A contact-polarized dermoscopy image of a skin lesion. A female subject approximately 35 years of age. The chart records no melanoma in first-degree relatives and no prior melanoma — 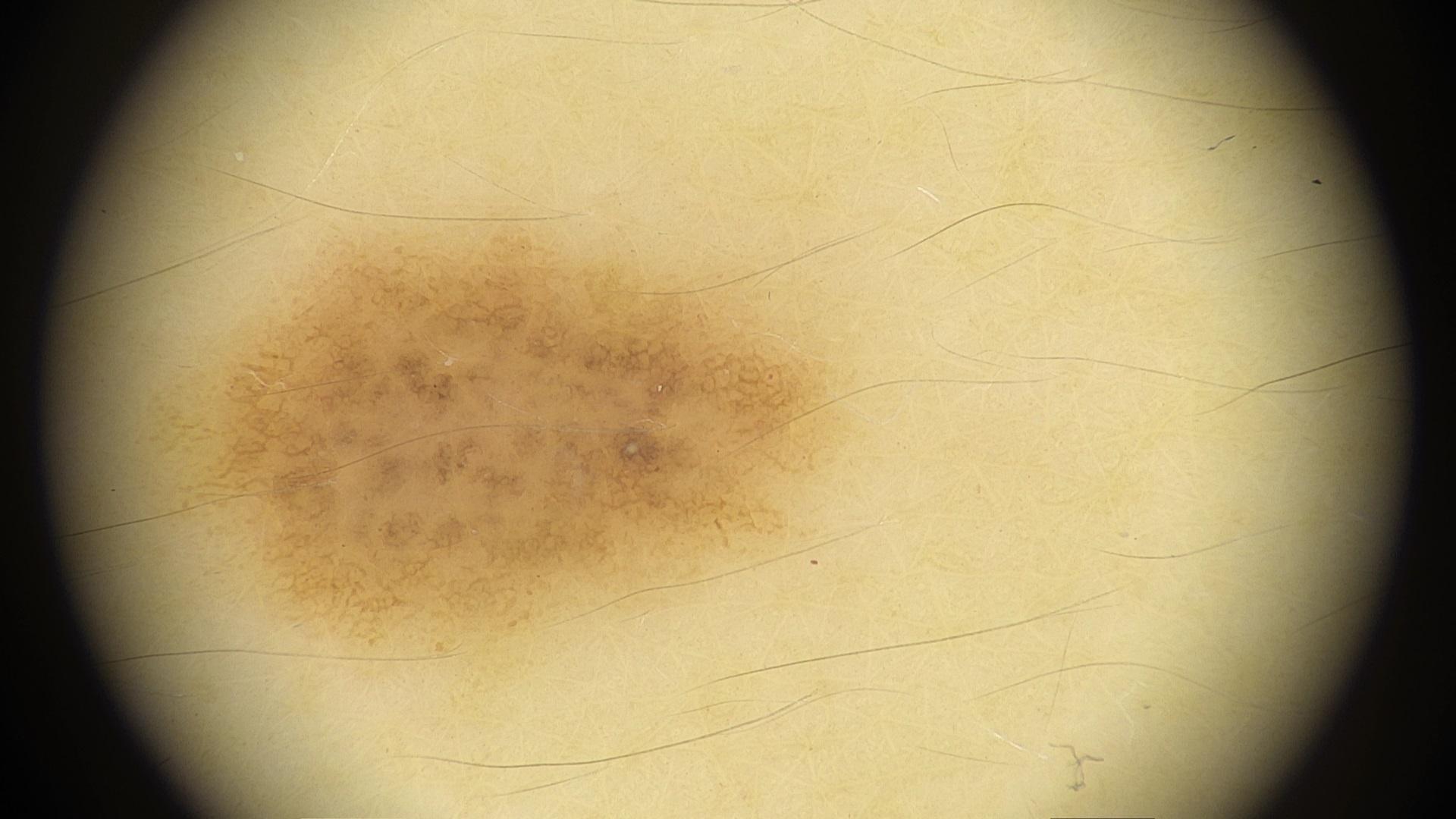{"lesion_location": {"region": "the trunk", "detail": "the posterior trunk"}, "diagnosis": {"name": "Nevus", "malignancy": "benign", "confirmation": "expert clinical impression", "lineage": "melanocytic"}}